The affected area is the arm; the photo was captured at a distance:
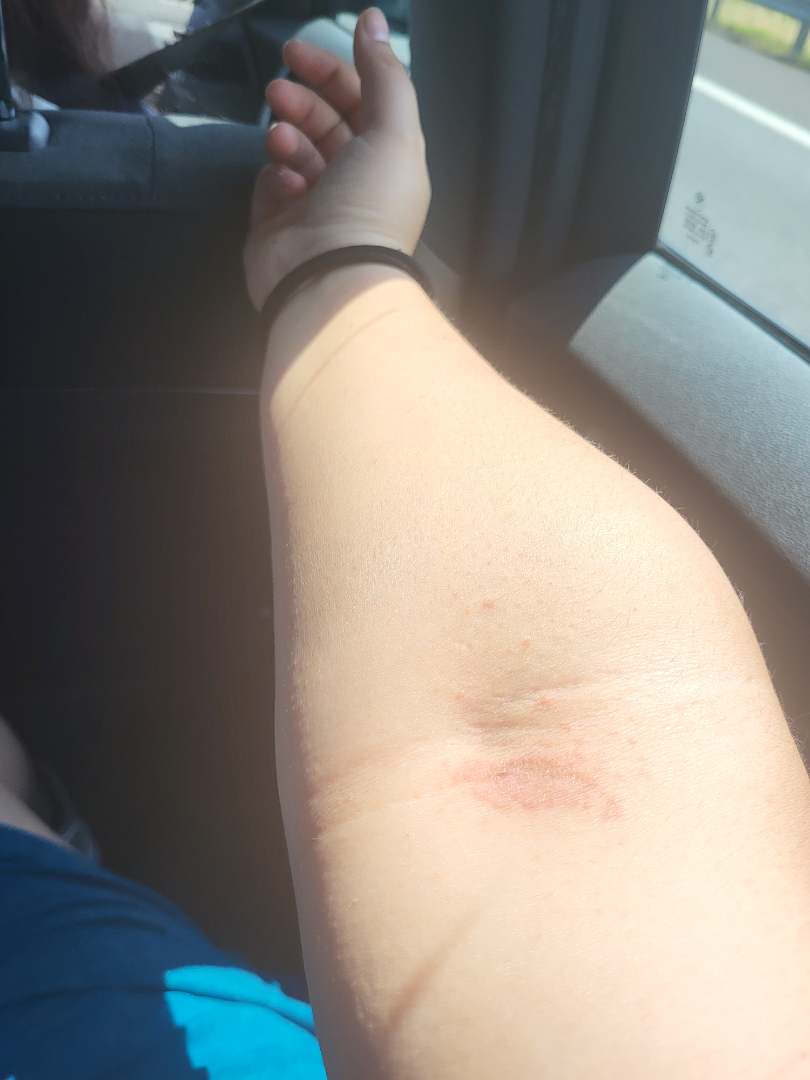Review:
The leading consideration is Eczema; also on the differential is Intertrigo; less probable is Tinea; less likely is Psoriasis.